A close-up photograph: 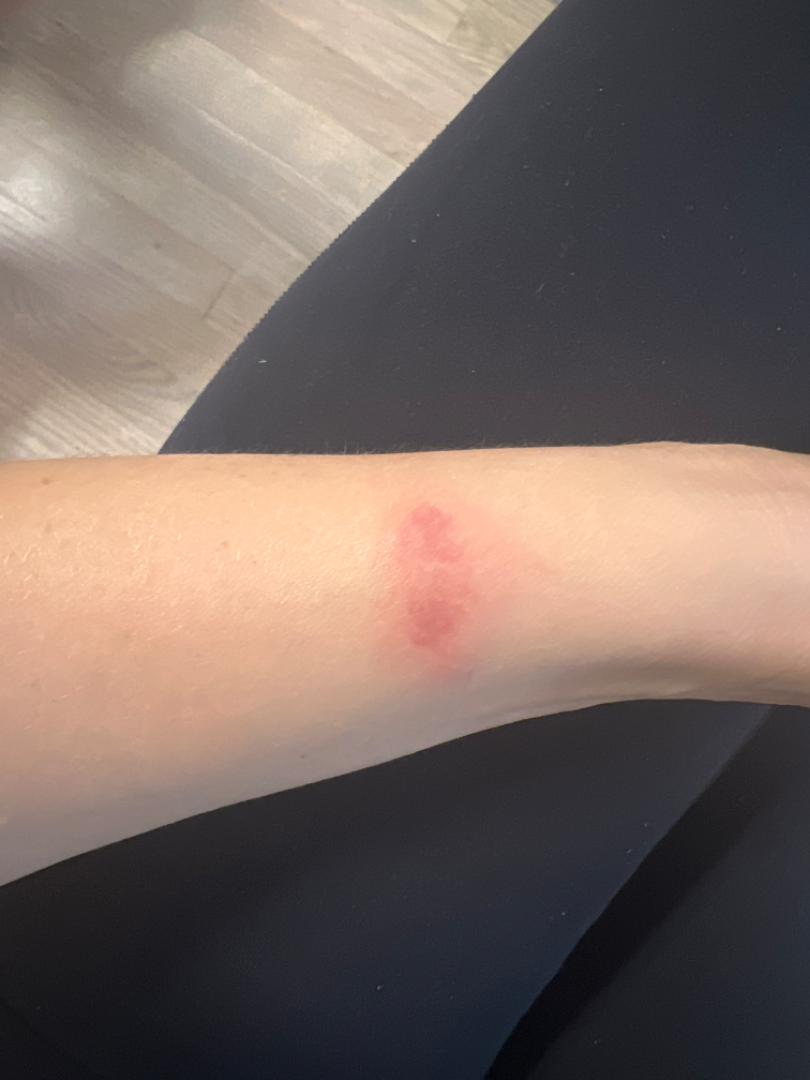Assessment:
Abrasion, scrape, or scab (possible); Insect Bite (possible); Allergic Contact Dermatitis (possible).